The lesion involves the palm, this image was taken at an angle:
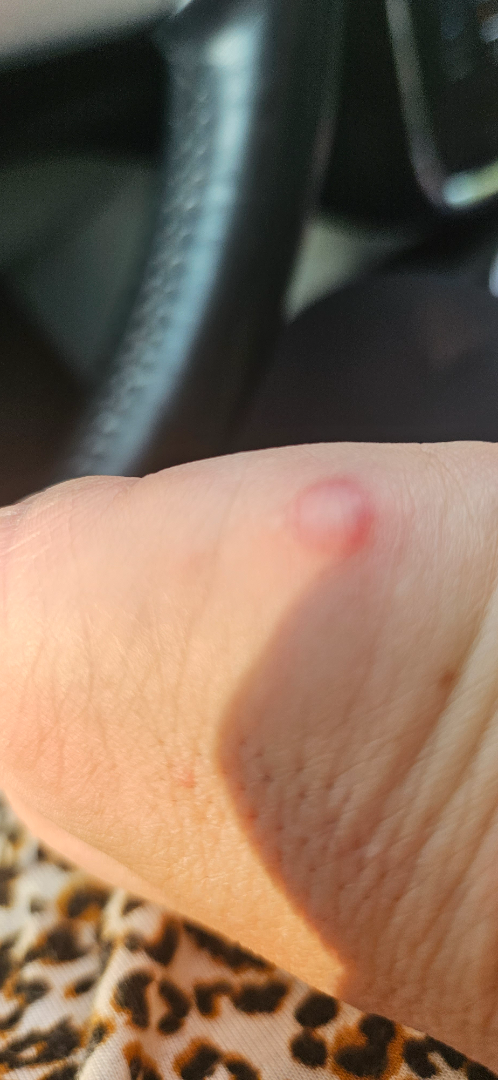A single dermatologist reviewed the case: most likely Herpes Simplex; also consider Skin and soft tissue atypical mycobacterial infection; an alternative is Eczema.